A dermoscopic close-up of a skin lesion: 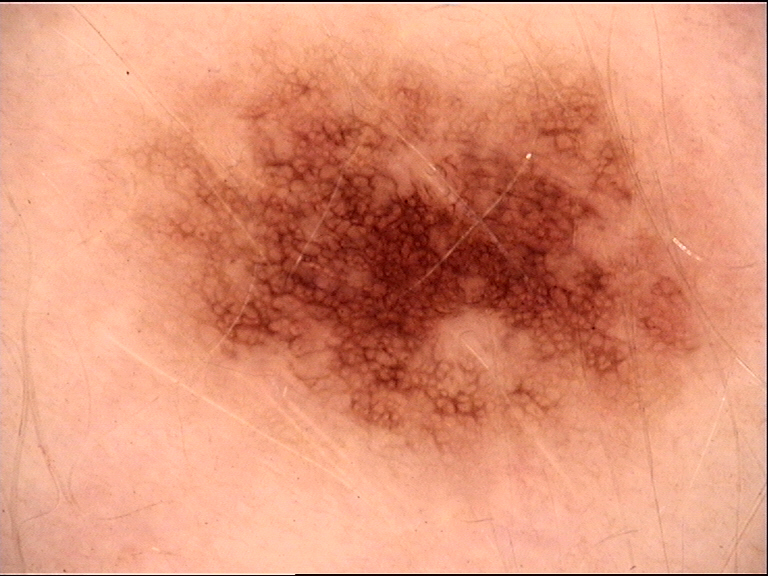diagnostic label: dysplastic junctional nevus (expert consensus).